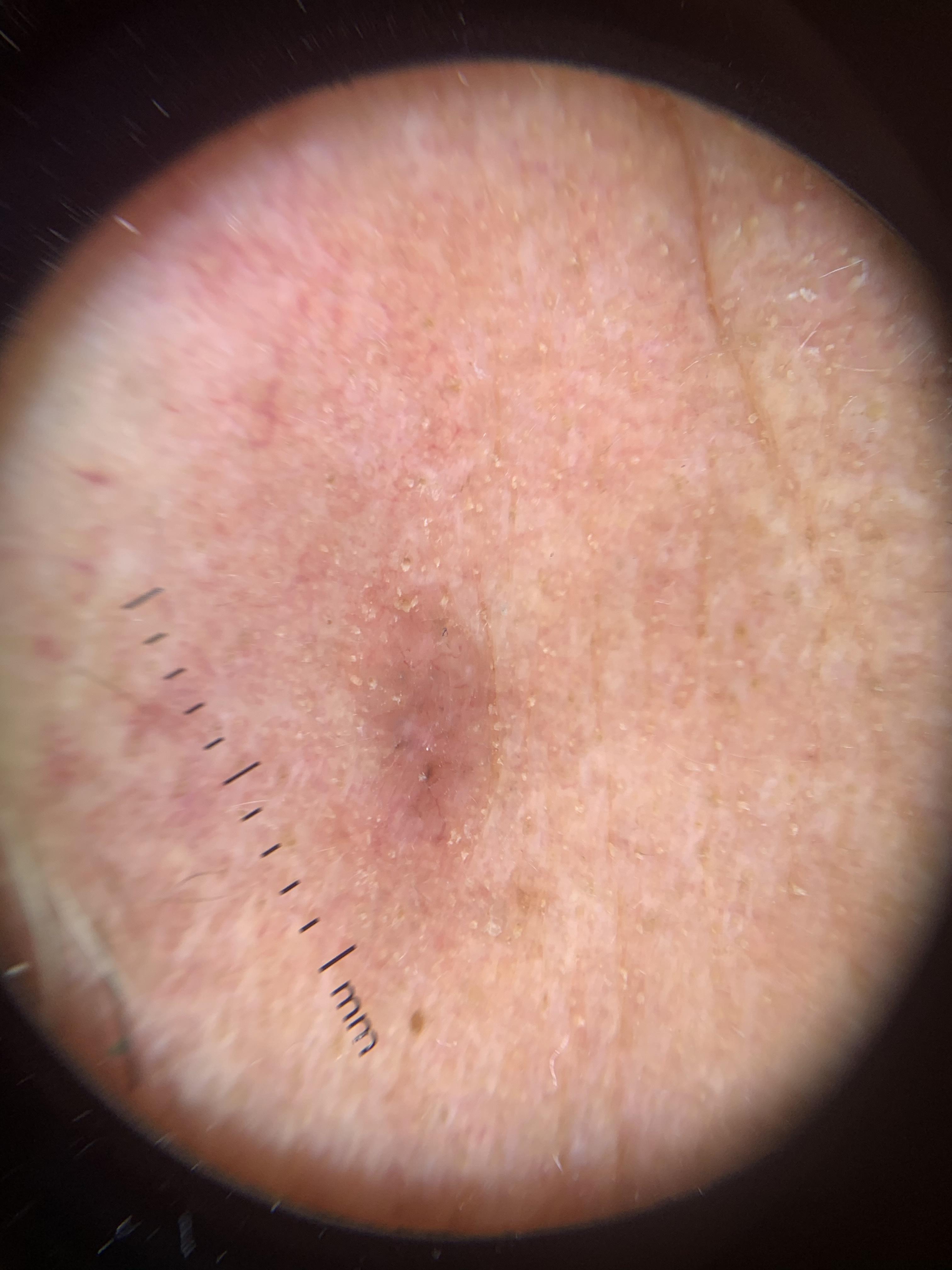Clinical context: Dermoscopy of a skin lesion. A male subject about 75 years old. The patient was assessed as Fitzpatrick skin type II. Located on the head or neck. Conclusion: Biopsy-confirmed as an adnexal lesion — a basal cell carcinoma.